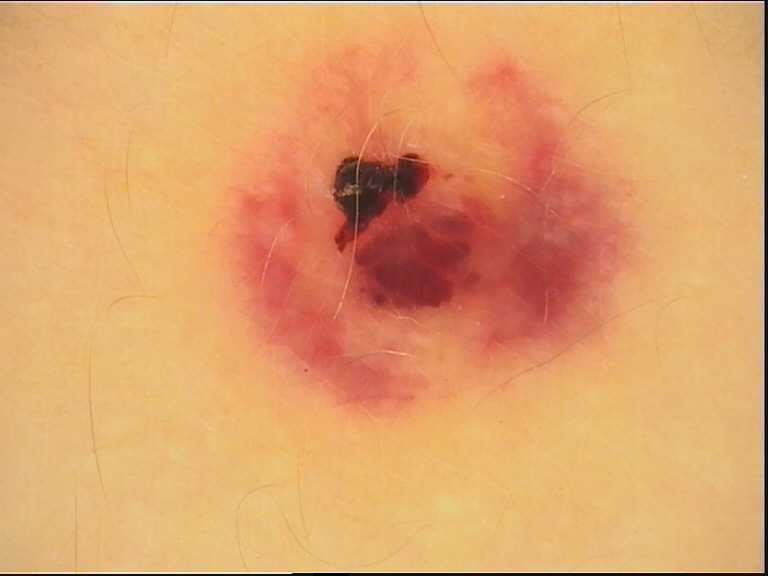A skin lesion imaged with a dermatoscope. This is a vascular lesion. Labeled as a hemangioma.